The chart notes prior malignancy (patient or family) and pesticide exposure · FST II · a clinical photograph of a skin lesion — 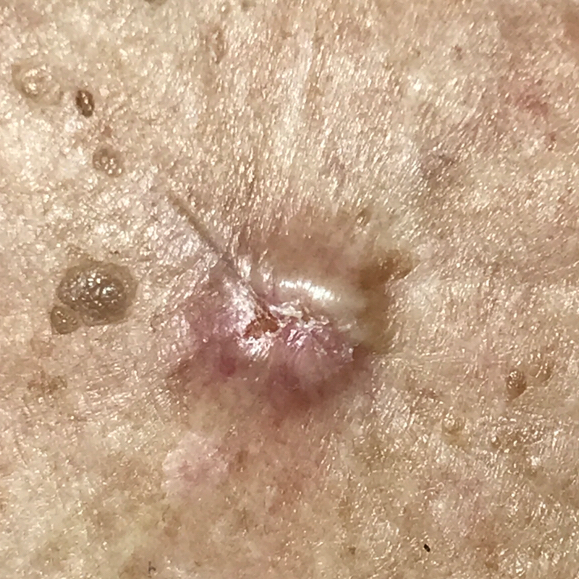Located on the chest.
The lesion measures 9 × 6 mm.
By the patient's account, the lesion hurts, has grown, itches, is elevated, and has changed, but has not bled.
Confirmed on histopathology as a malignant lesion — a basal cell carcinoma.